Dermoscopy of a skin lesion:
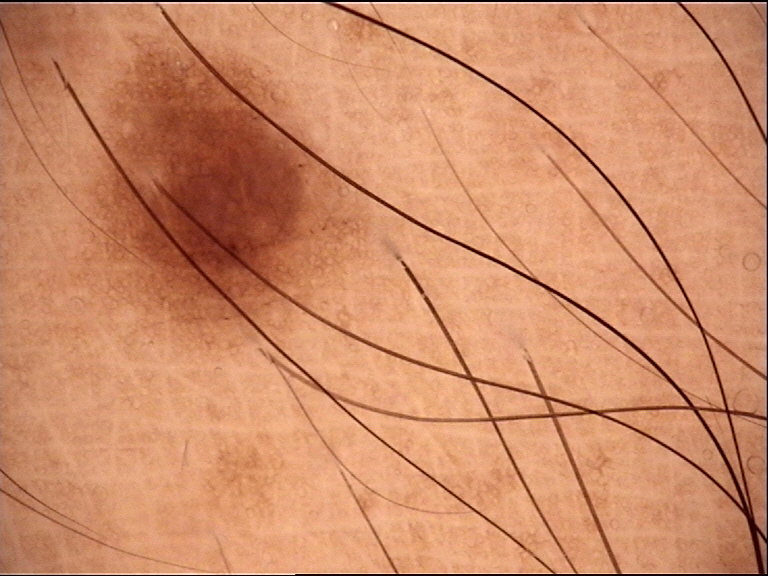lesion_type:
  main_class: banal
  pattern: junctional
diagnosis:
  name: junctional nevus
  code: jb
  malignancy: benign
  super_class: melanocytic
  confirmation: expert consensus